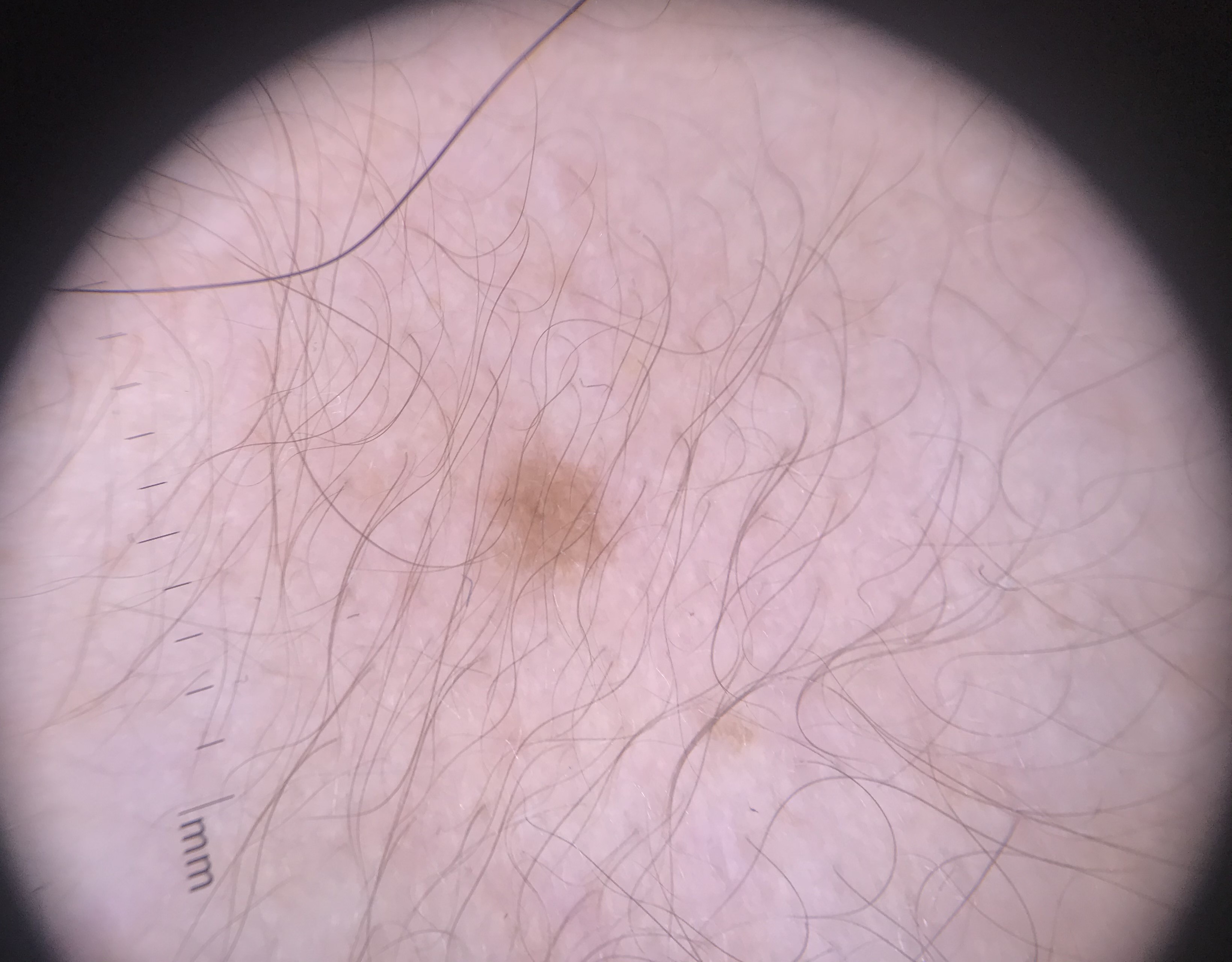The diagnostic label was a benign lesion — a seborrheic keratosis.